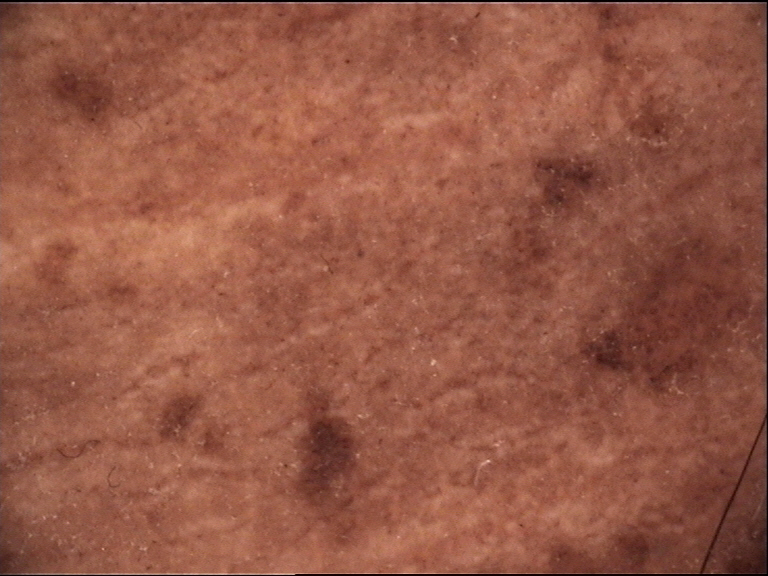A skin lesion imaged with a dermatoscope.
The diagnostic label was a banal lesion — a congenital compound nevus.